A subject in their 40s; a clinical photograph showing a skin lesion — 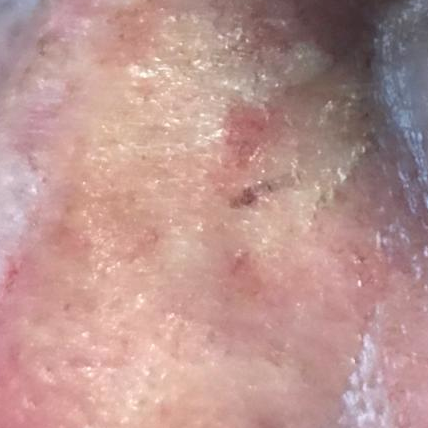Summary: The lesion is on the nose. The patient reports that the lesion itches. Conclusion: Expert review favored an actinic keratosis.